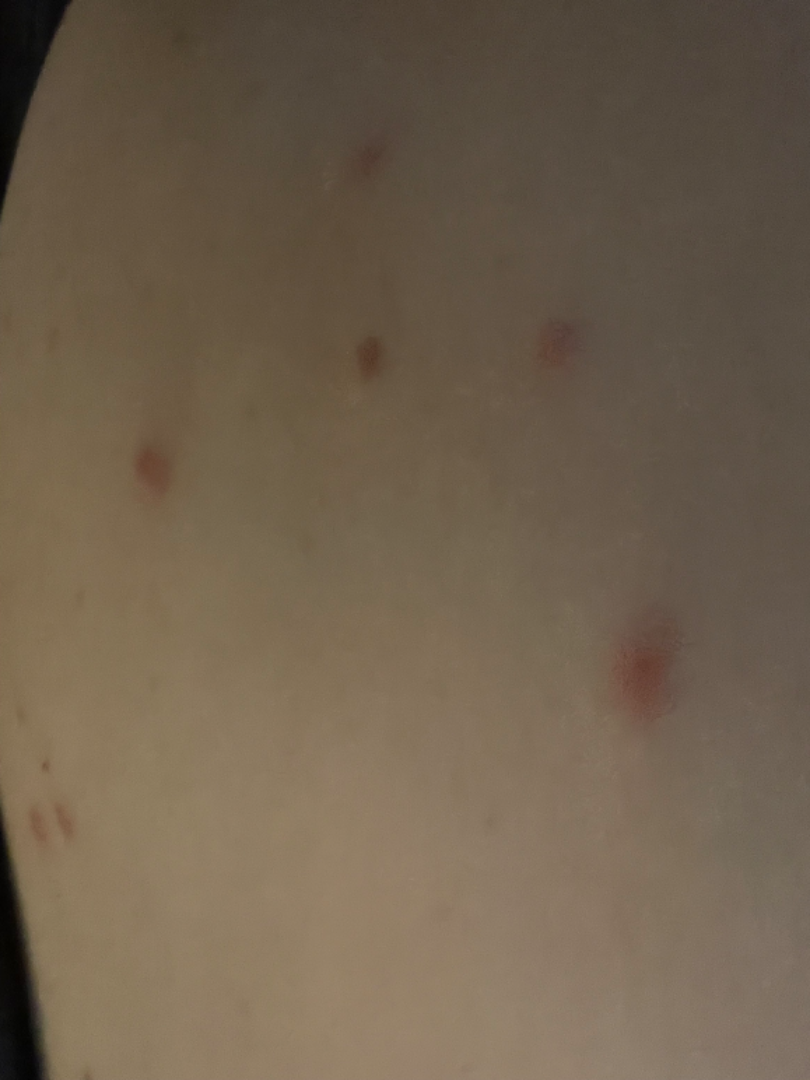{
  "body_site": [
    "back of the torso",
    "front of the torso"
  ],
  "texture": [
    "raised or bumpy",
    "fluid-filled"
  ],
  "systemic_symptoms": "fatigue",
  "shot_type": "close-up",
  "patient": "female, age 40–49",
  "differential": {
    "Folliculitis": 0.41,
    "Insect Bite": 0.41,
    "Cyst": 0.18
  }
}